A dermoscopic photograph of a skin lesion:
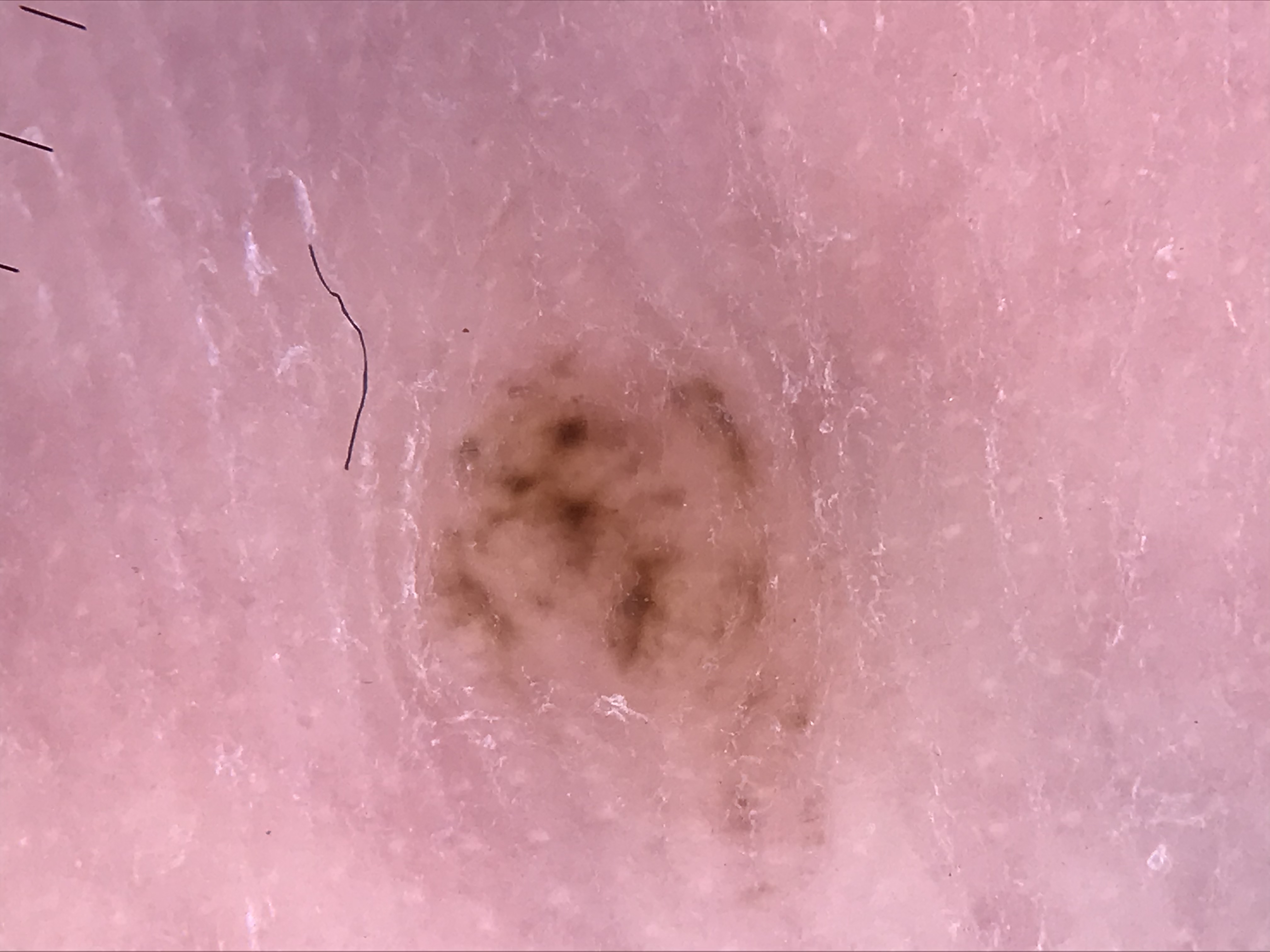subtype: banal
diagnostic label: acral compound nevus (expert consensus)